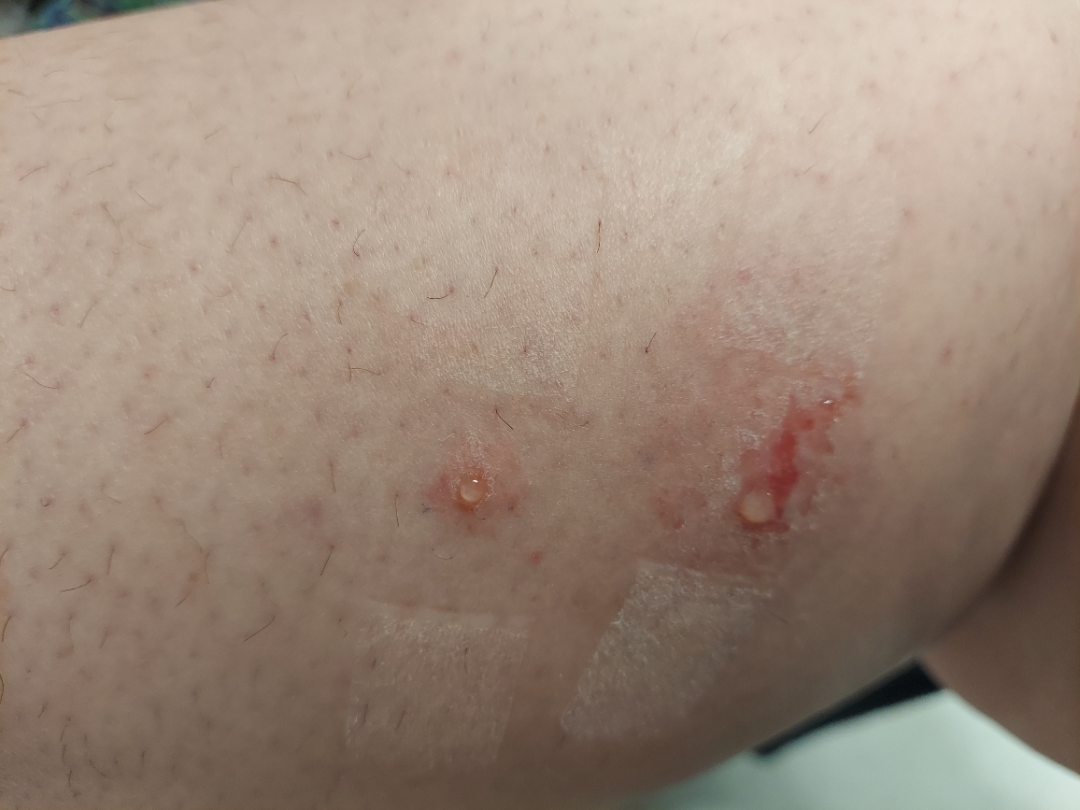The image was not sufficient for the reviewer to characterize the skin condition. Reported lesion symptoms include itching, enlargement and bothersome appearance. Located on the leg. Close-up view. The contributor reports the condition has been present for less than one week. Female contributor, age 18–29. The contributor reports associated fatigue and chills. Texture is reported as rough or flaky. The patient considered this a rash.